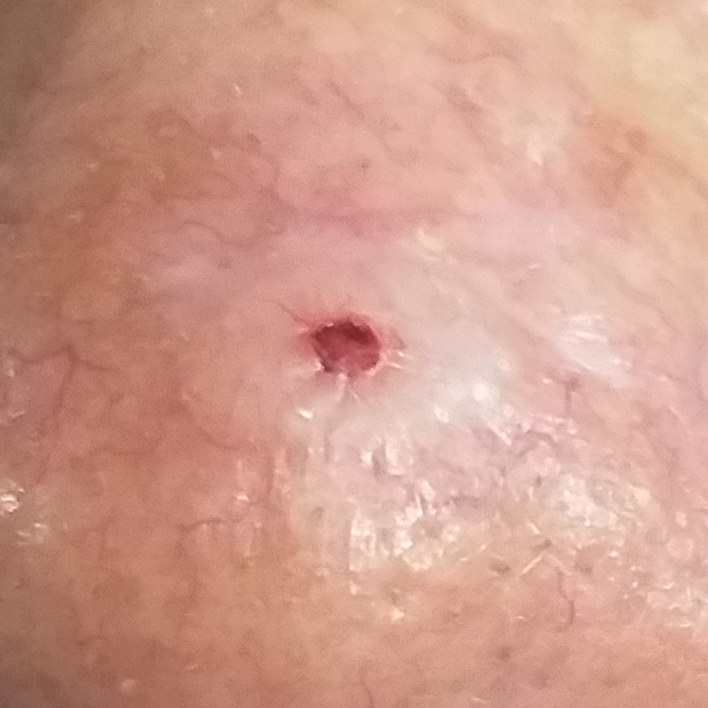patient: female, age 57
imaging: clinical photograph
Fitzpatrick: III
lesion size: approx. 12 × 9 mm
reported symptoms: pain, growth, bleeding, itching, elevation / no change in appearance
diagnostic label: basal cell carcinoma (biopsy-proven)